The photograph is a close-up of the affected area:
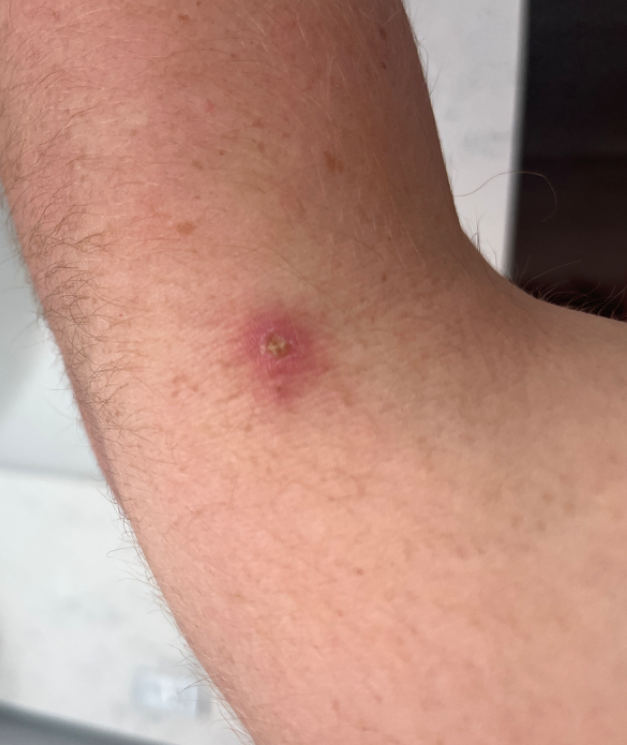The differential, in no particular order, includes Ecthyma and Abscess.